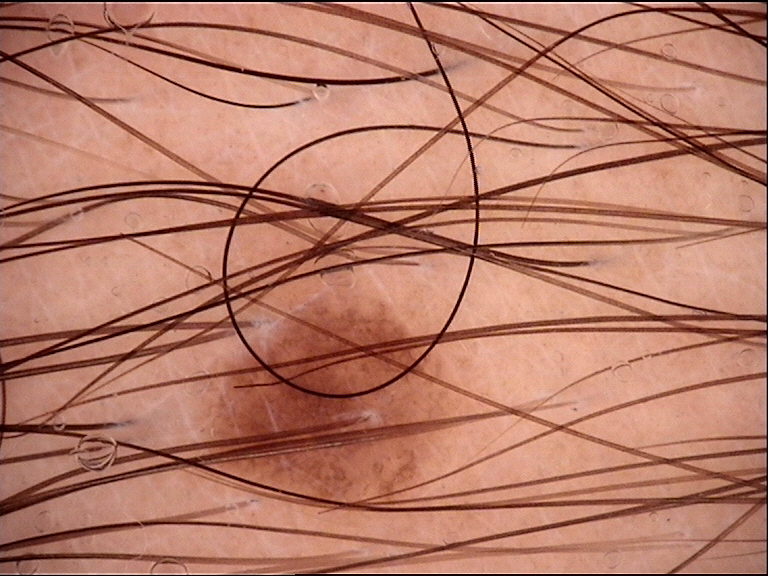A dermoscopic close-up of a skin lesion. The diagnostic label was a benign lesion — a dysplastic junctional nevus.